Dermoscopy of a skin lesion: 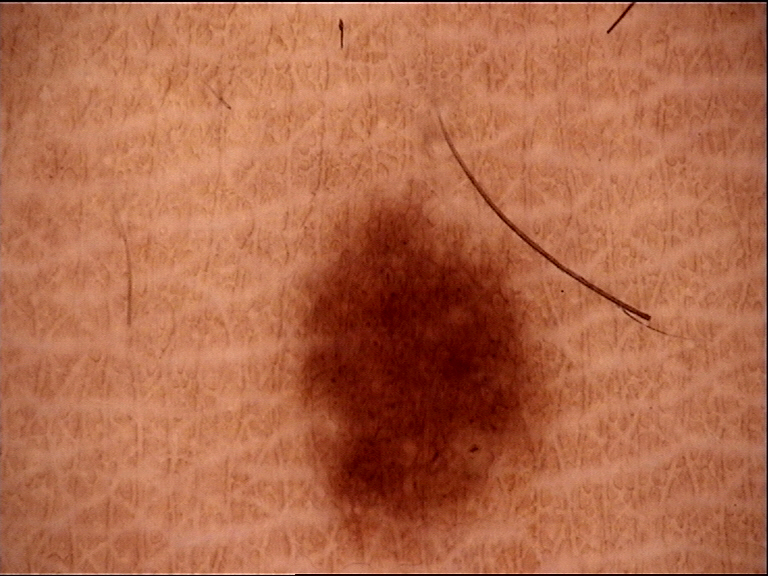The architecture is that of a banal lesion. Diagnosed as a junctional nevus.